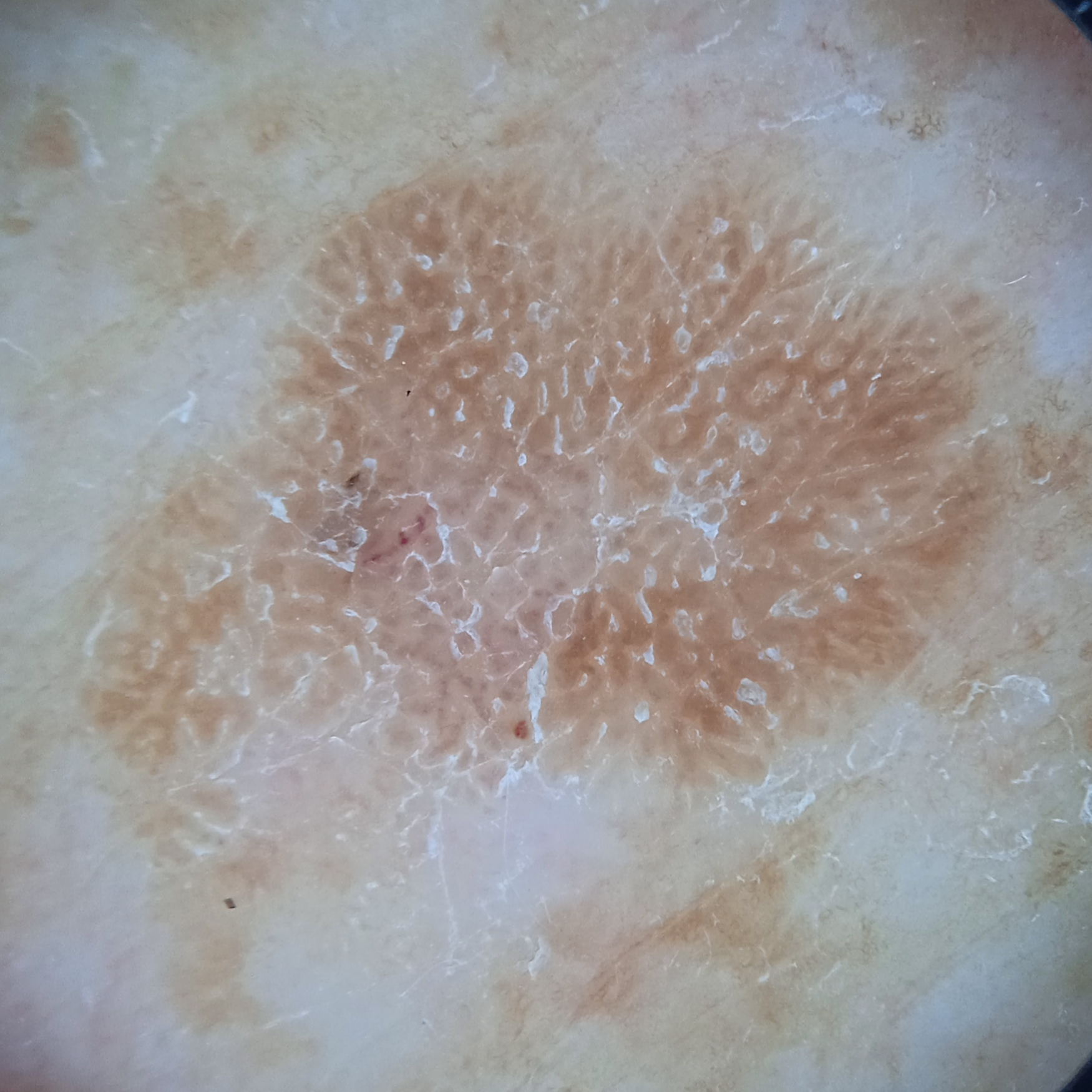nevus count: numerous melanocytic nevi; sun reaction: skin reddens with sun exposure; clinical context: research study (no referral diagnosis); diameter: 10.7 mm; diagnosis: seborrheic keratosis (dermatologist consensus).